A male patient age 77 · acquired for a research image collection, with no referral diagnosis · a moderate number of moles by the patient's own estimate · a dermoscopy image of a skin lesion · the patient says their skin reddens with sun exposure · by self-report, a personal history of cancer and a personal history of skin cancer: 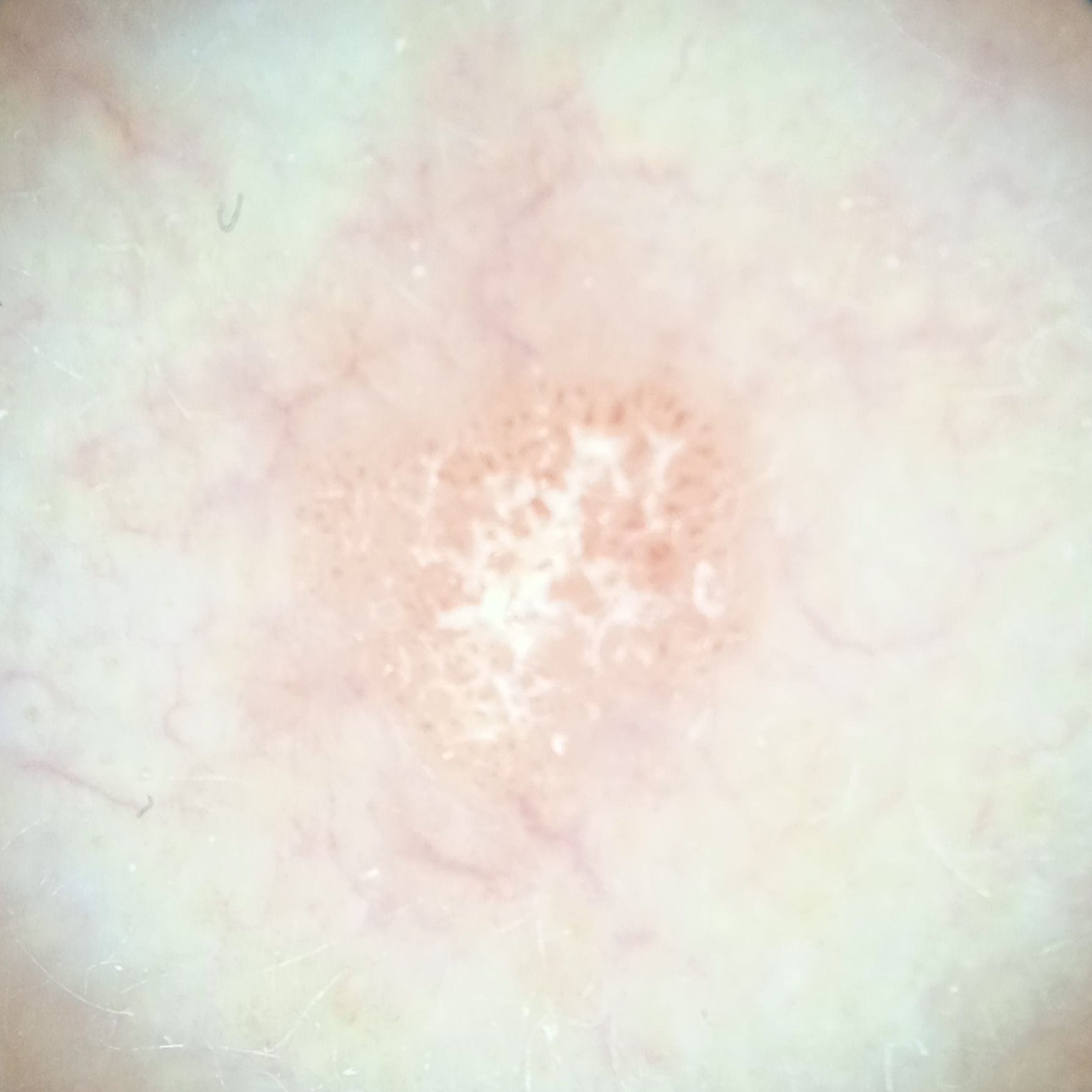Clinical context: The lesion is located on the face. Measuring roughly 4.3 mm. Impression: The consensus diagnosis for this lesion was an actinic keratosis.